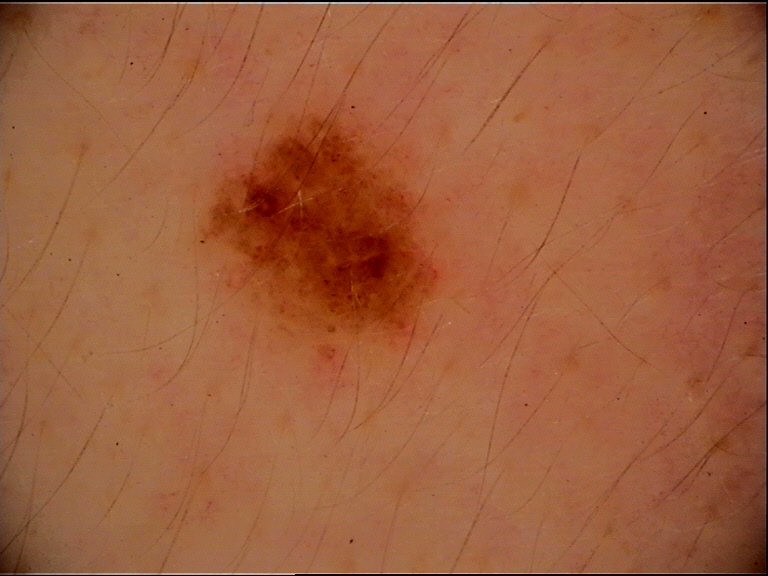Findings:
A dermatoscopic image of a skin lesion.
Impression:
The diagnostic label was a dysplastic junctional nevus.